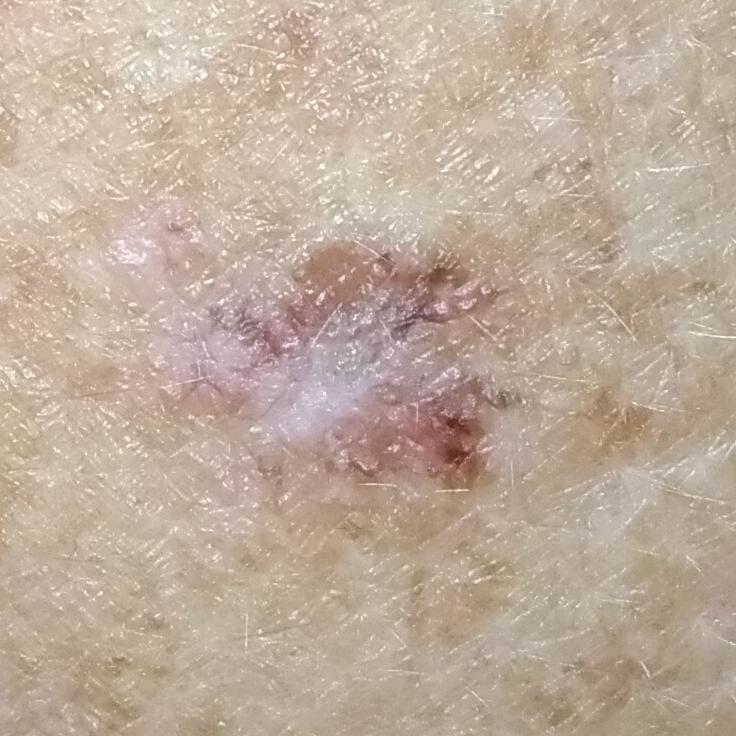On biopsy, the diagnosis was a basal cell carcinoma.